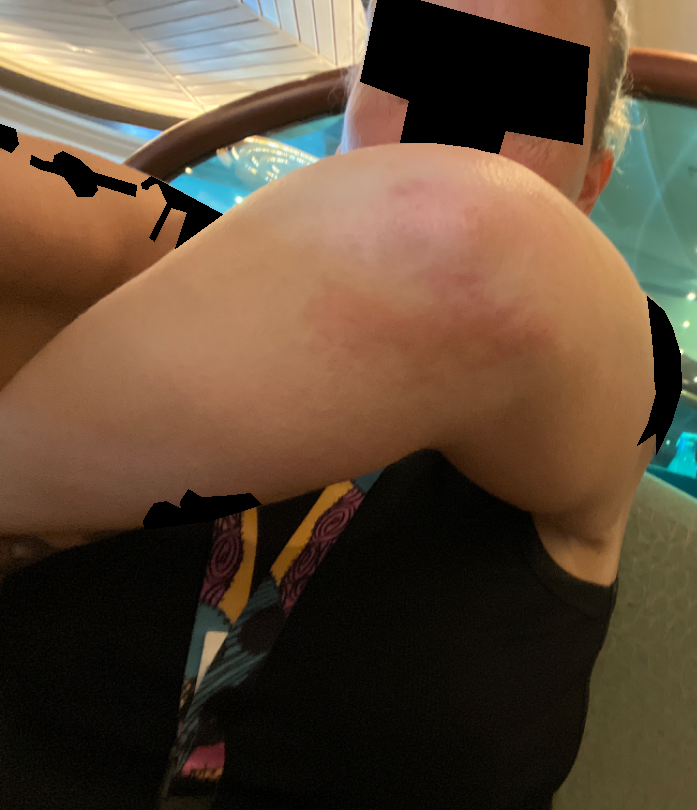Background: The photo was captured at a distance. Symptoms reported: itching. Skin tone: Fitzpatrick II. The lesion is described as raised or bumpy. The affected area is the arm. Female contributor, age 40–49. Findings: Reviewed remotely by three dermatologists: the favored diagnosis is Allergic Contact Dermatitis; also consider Urticaria; with consideration of Eczema; less probable is Dermatitis herpetiformis.